A clinical close-up photograph of a skin lesion · a patient aged 69:
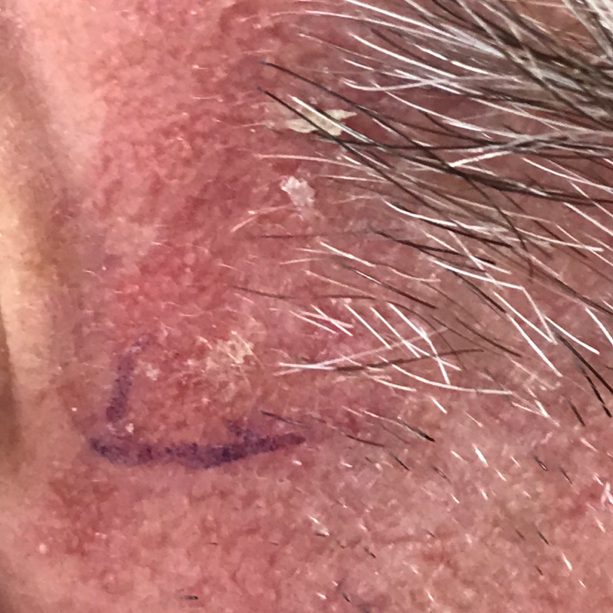Patient and lesion: The lesion was found on an ear. By the patient's account, the lesion itches. Conclusion: The clinical impression was an actinic keratosis.